A dermoscopic image of a skin lesion.
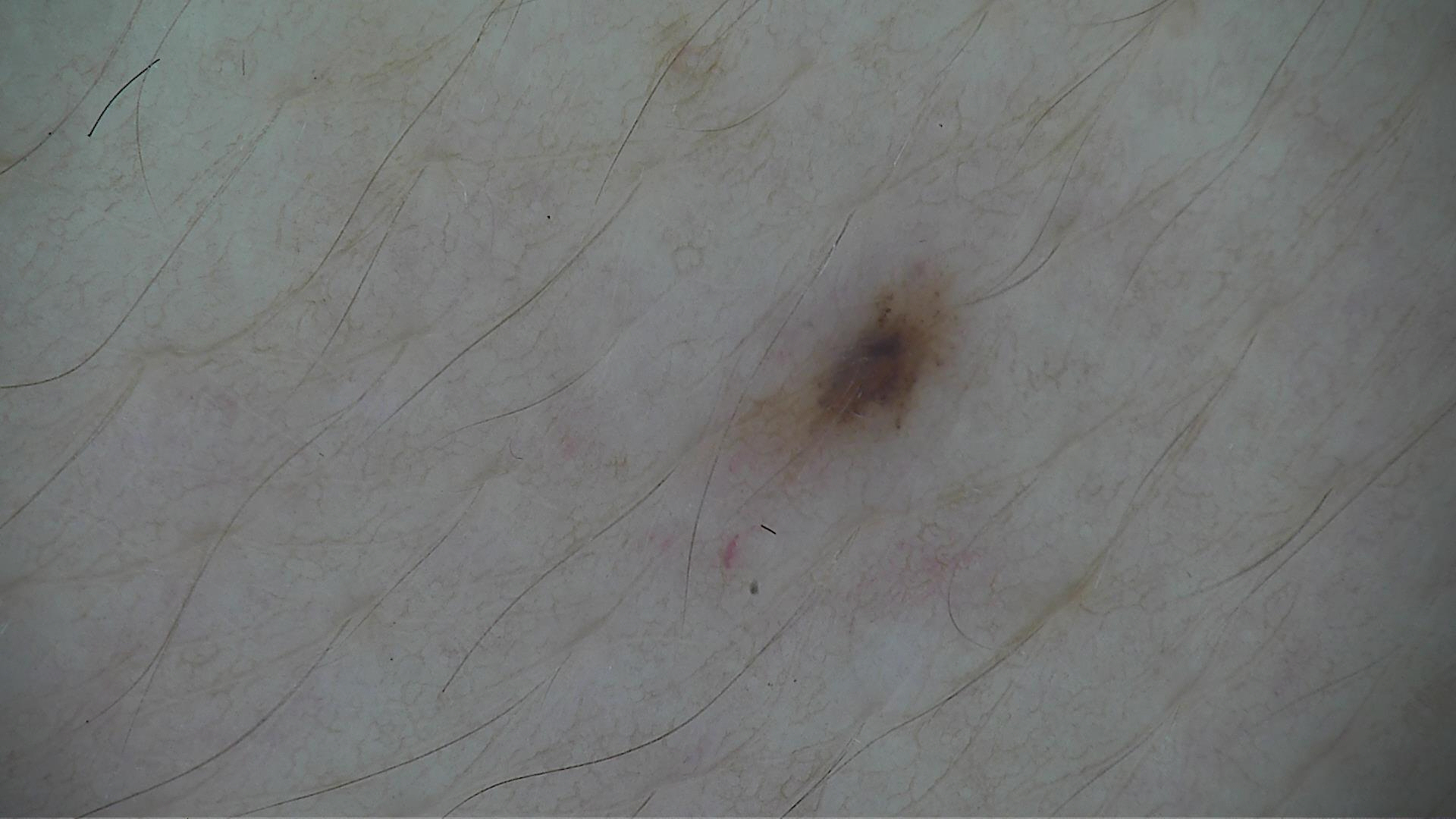Consistent with a dysplastic junctional nevus.